Dermoscopy of a skin lesion: 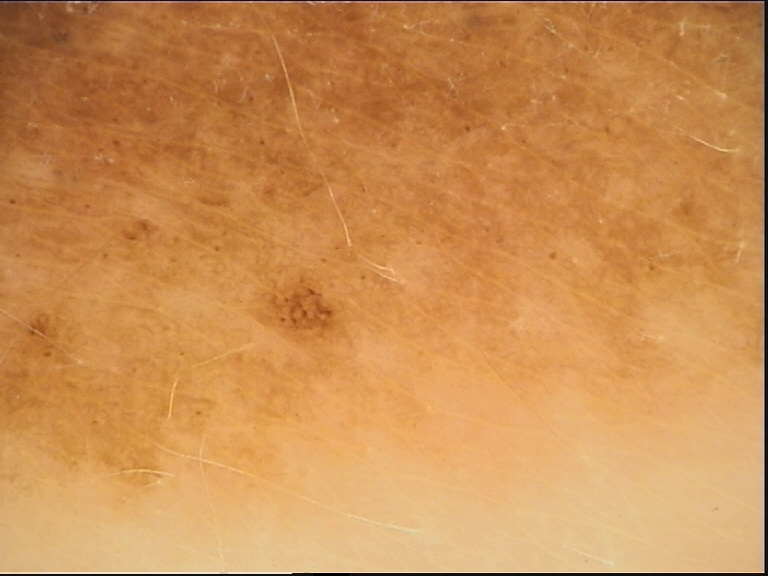Findings:
– diagnosis — congenital junctional nevus (expert consensus)